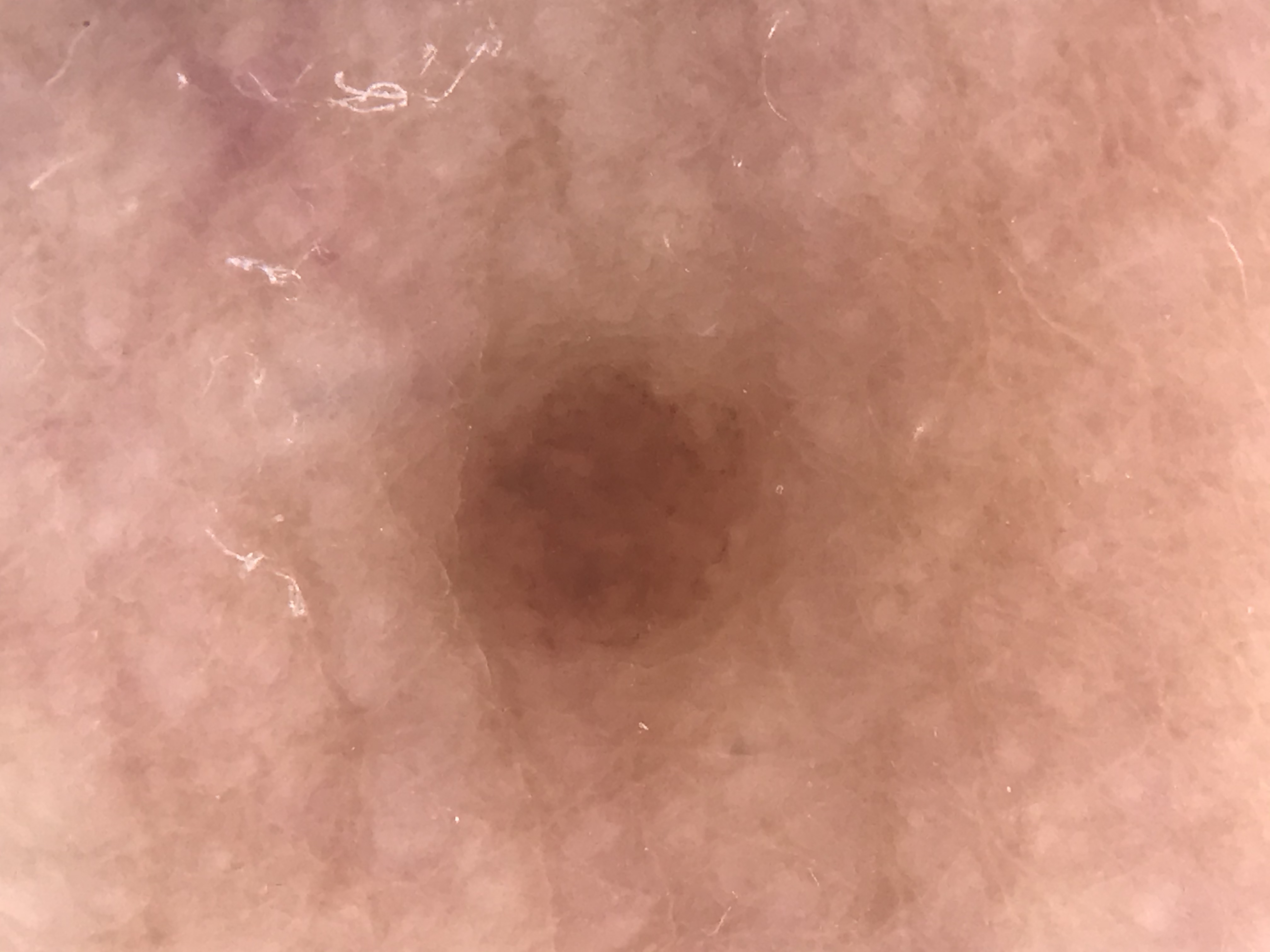Summary: A dermatoscopic image of a skin lesion. The architecture is that of a banal lesion. Conclusion: Diagnosed as a junctional nevus.